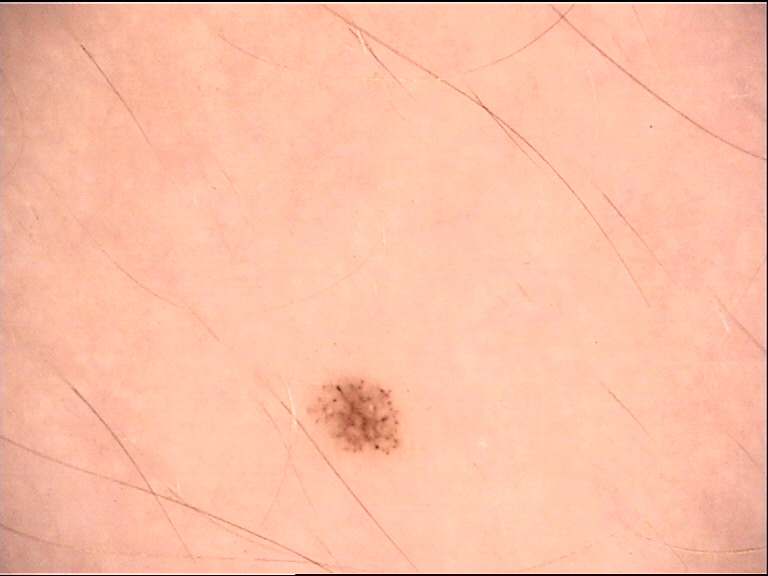{
  "diagnosis": {
    "name": "dysplastic junctional nevus",
    "code": "jd",
    "malignancy": "benign",
    "super_class": "melanocytic",
    "confirmation": "expert consensus"
  }
}